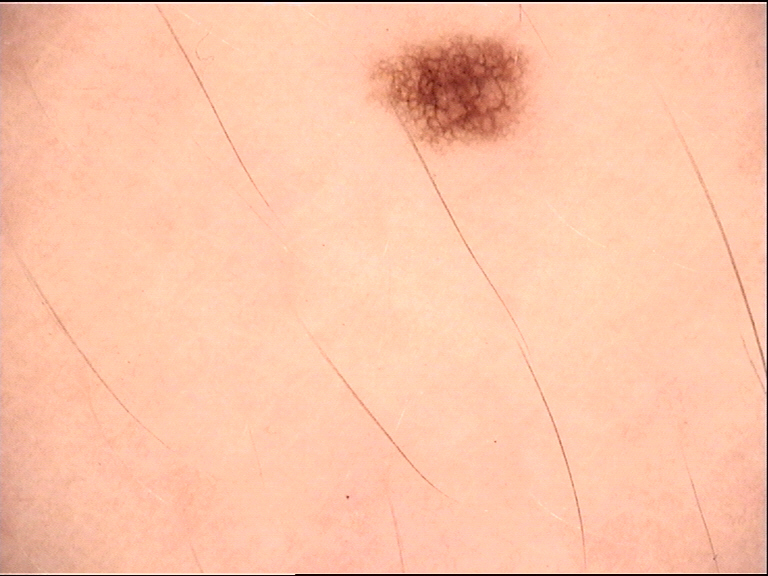The diagnostic label was a dysplastic junctional nevus.